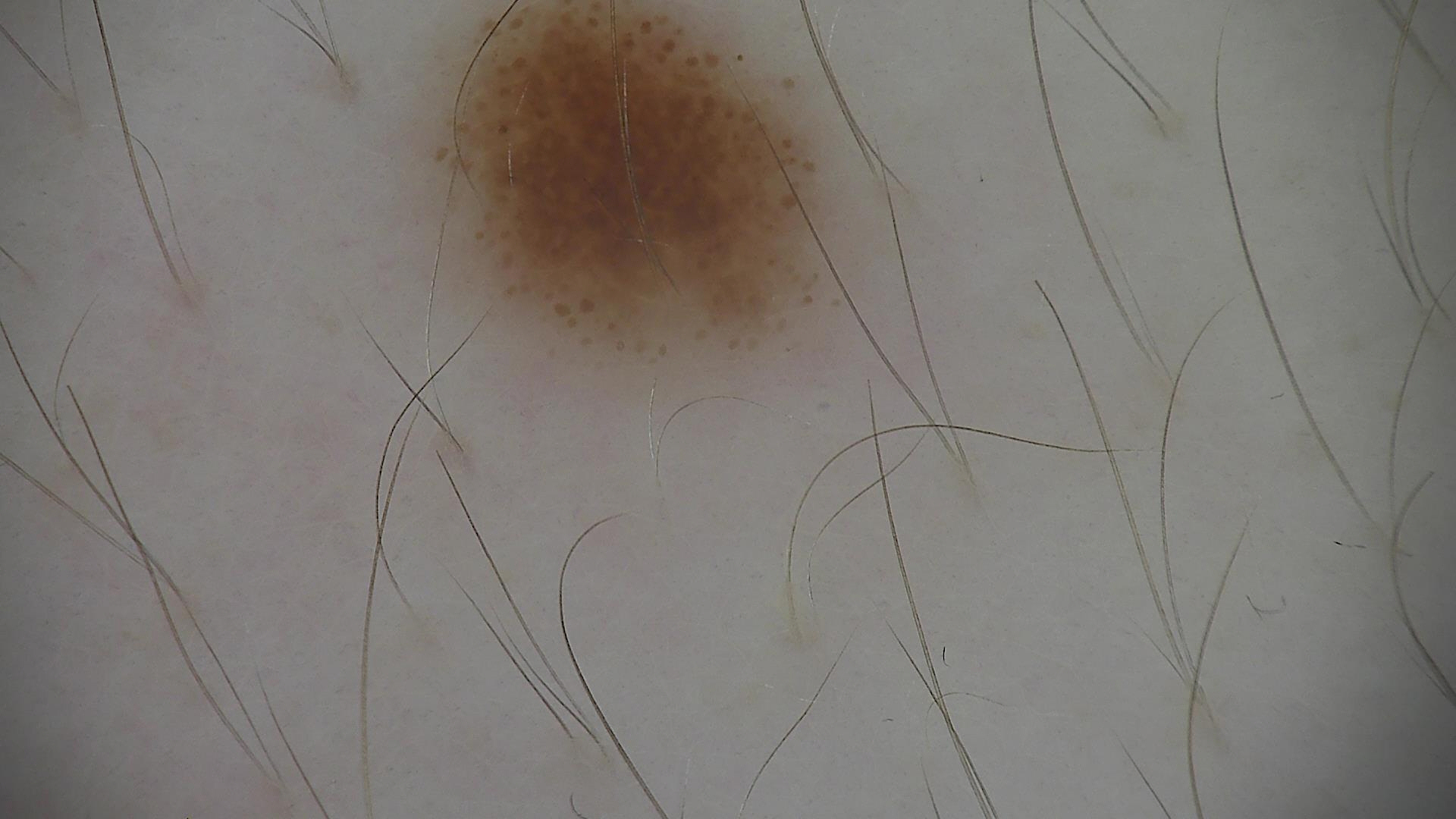{
  "image": "dermatoscopy",
  "diagnosis": {
    "name": "dysplastic junctional nevus",
    "code": "jd",
    "malignancy": "benign",
    "super_class": "melanocytic",
    "confirmation": "expert consensus"
  }
}